The patient described the issue as a rash. Symptoms reported: burning, itching, enlargement and bothersome appearance. Skin tone: Fitzpatrick skin type III. No constitutional symptoms were reported. This image was taken at a distance. Reported duration is one to four weeks. The contributor reports the lesion is fluid-filled and raised or bumpy. The leg, arm and back of the torso are involved: 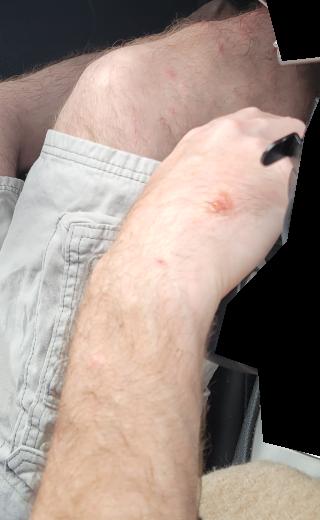Findings:
• diagnostic considerations · consistent with Allergic Contact Dermatitis